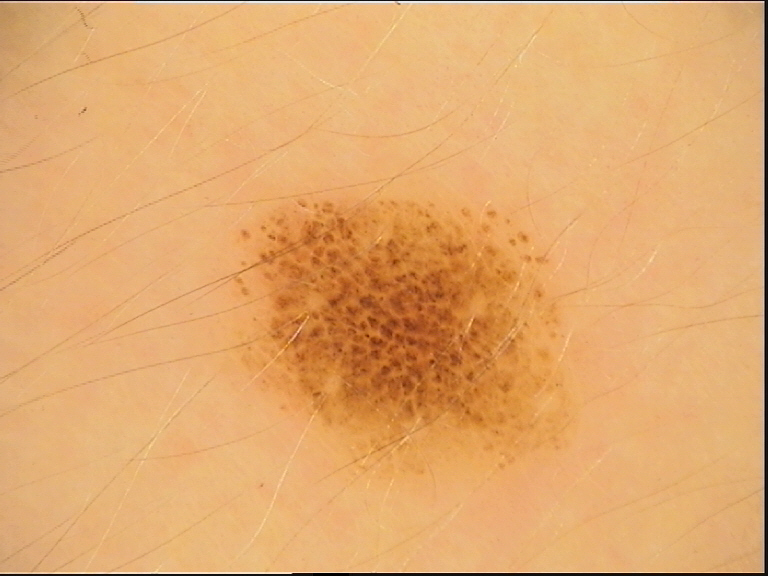A dermoscopic photograph of a skin lesion. Diagnosed as a banal lesion — a compound nevus.